Acquired for a research image collection, with no referral diagnosis · the patient describes having few moles overall · by self-report, no immunosuppression and no personal history of cancer · the patient says their skin reddens with sun exposure · a clinical close-up of a skin lesion · a male subject aged 62: 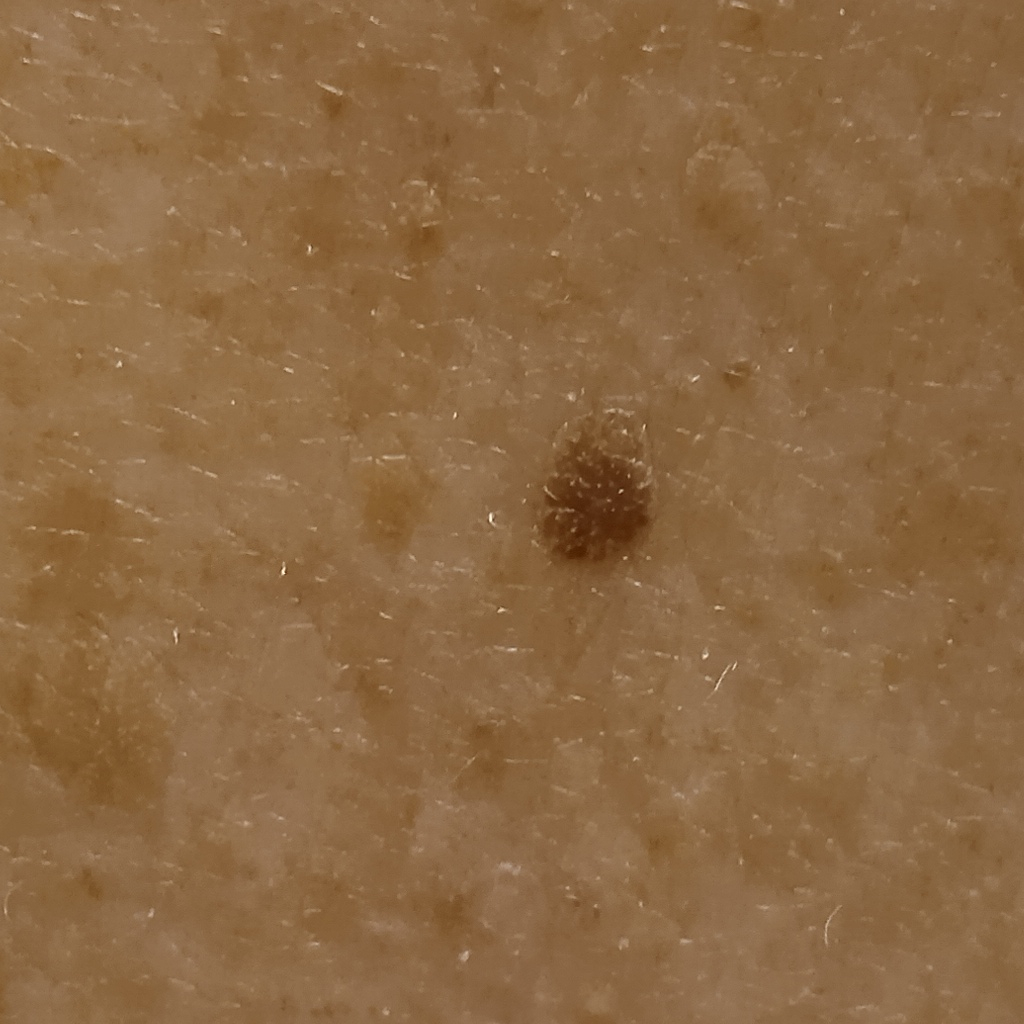Q: What is the anatomic site?
A: the back
Q: How large is the lesion?
A: 4.3 mm
Q: What was the diagnosis?
A: seborrheic keratosis (dermatologist consensus)